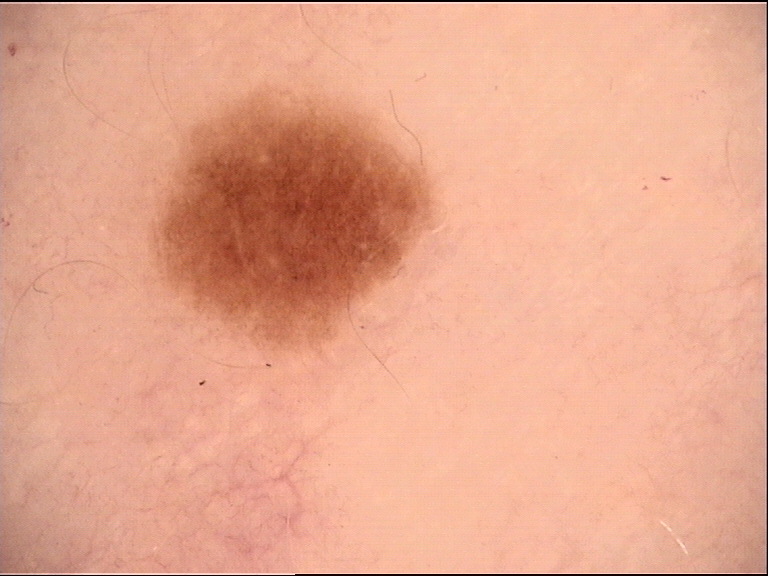assessment: junctional nevus (expert consensus).